A clinical photo of a skin lesion taken with a smartphone; a subject in their early 50s: 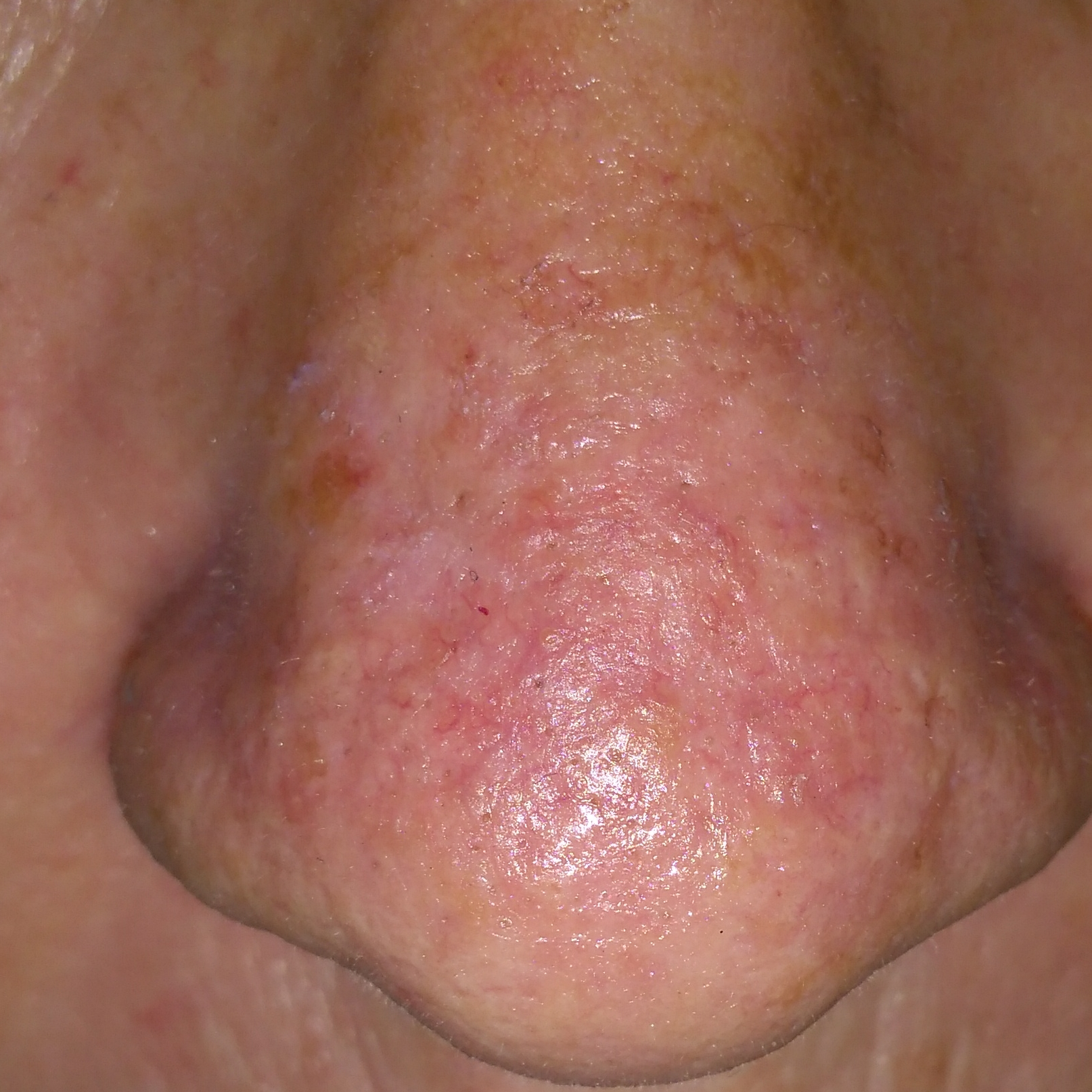The lesion involves the nose.
The patient describes that the lesion itches.
Diagnosed by dermatologist consensus as an actinic keratosis.